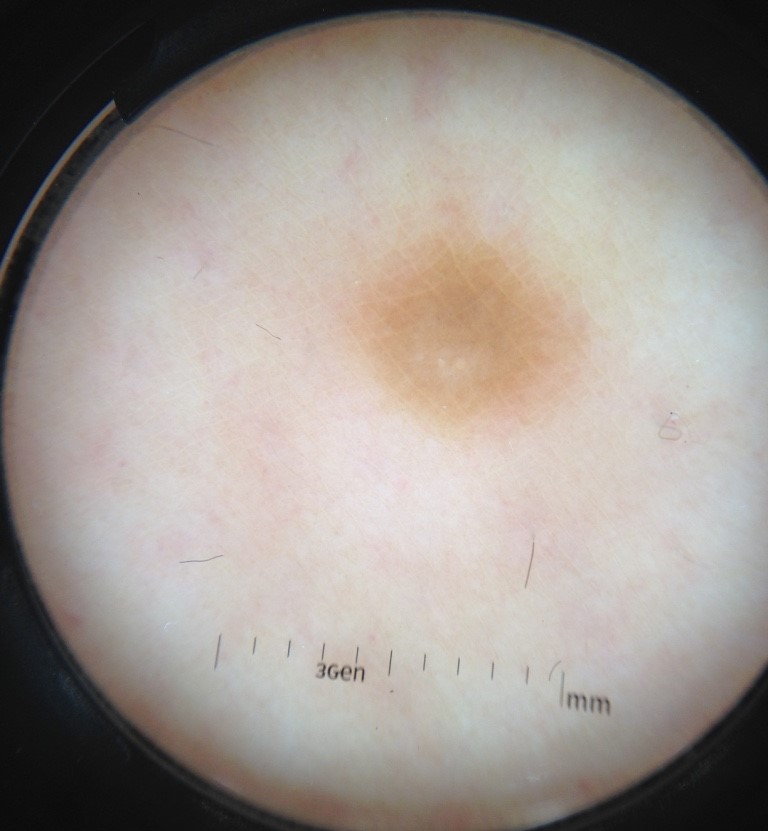Case:
A skin lesion imaged with a dermatoscope.
Conclusion:
Classified as a fibro-histiocytic, benign lesion — a dermatofibroma.